A dermoscopic image of a skin lesion.
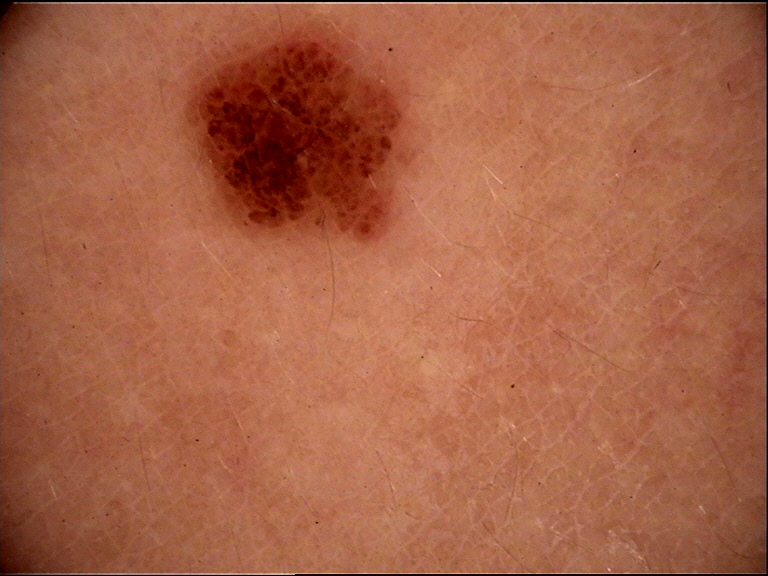Conclusion: Labeled as a banal lesion — a compound nevus.